A skin lesion imaged with a dermatoscope.
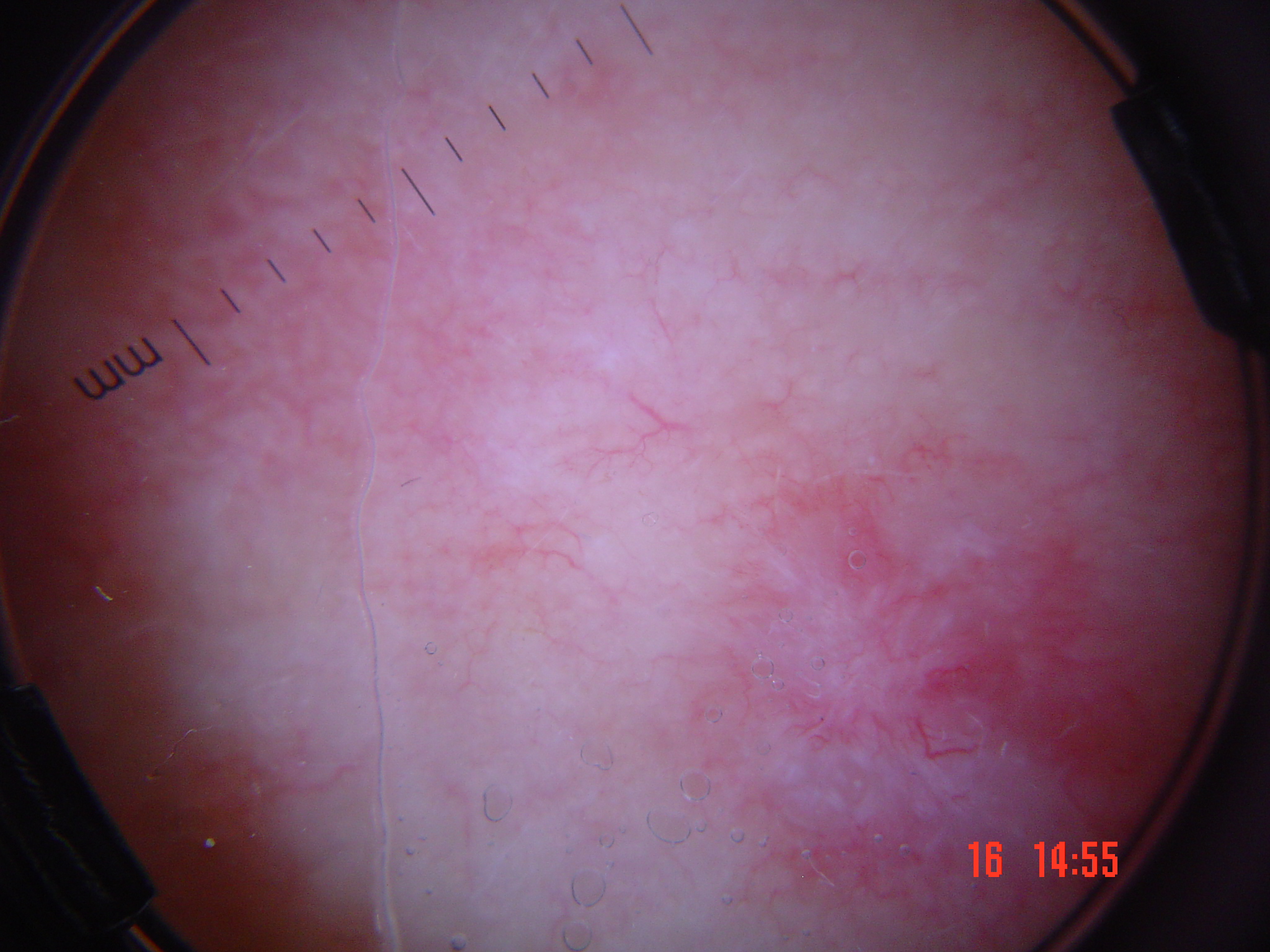This is a keratinocytic lesion. The biopsy diagnosis was a squamous cell carcinoma.